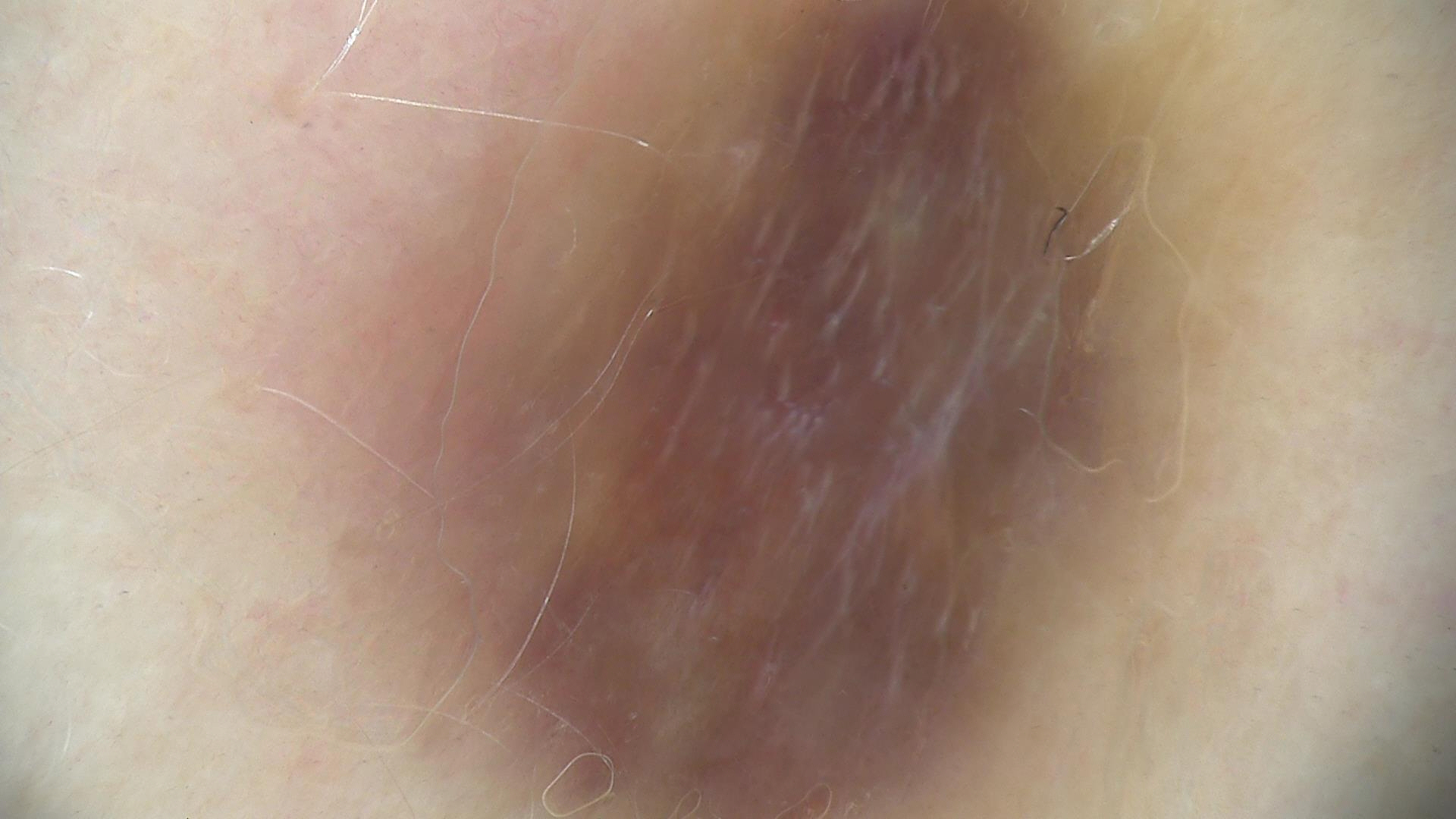{"image": "dermoscopy", "lesion_type": {"main_class": "banal", "pattern": "dermal"}, "diagnosis": {"name": "blue nevus", "code": "bdb", "malignancy": "benign", "super_class": "melanocytic", "confirmation": "expert consensus"}}